Located on the palm; the photograph is a close-up of the affected area: 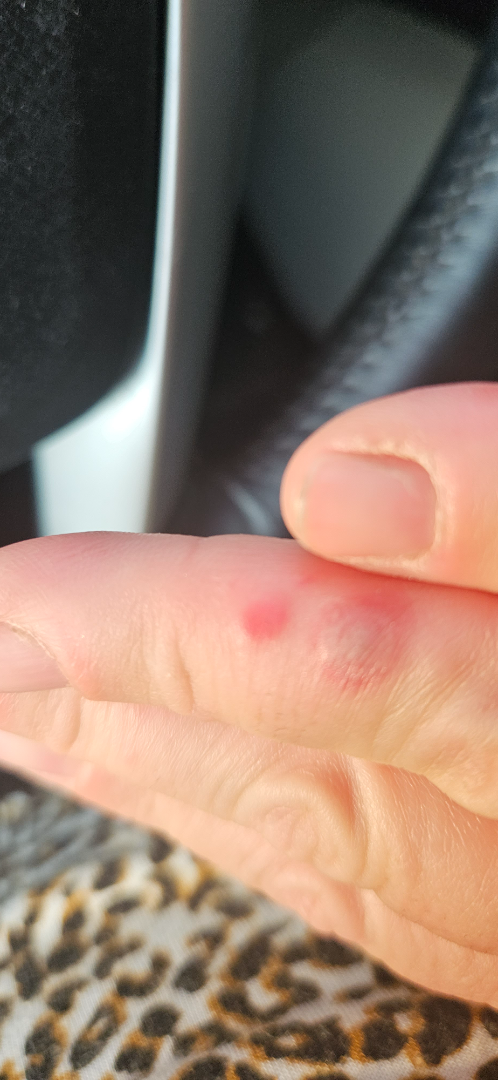Herpes Simplex (favored); Skin and soft tissue atypical mycobacterial infection (possible); Eczema (possible).